Dermoscopy of a skin lesion.
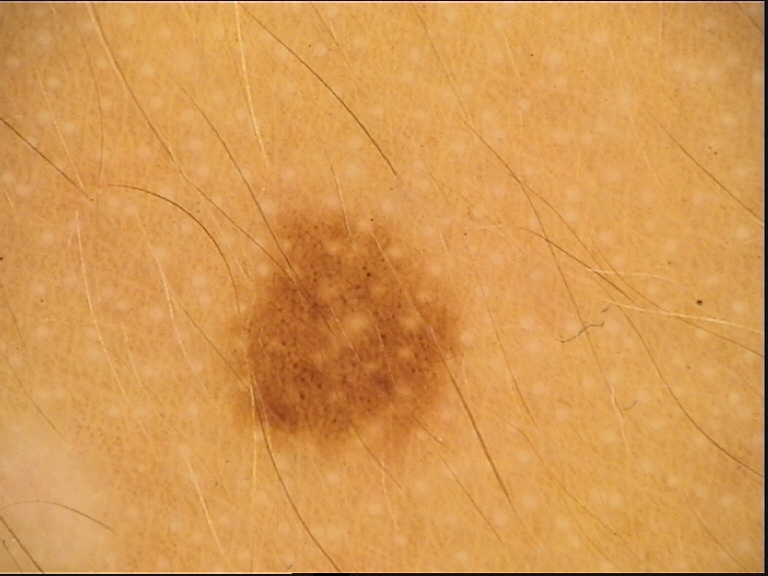label: compound nevus (expert consensus).